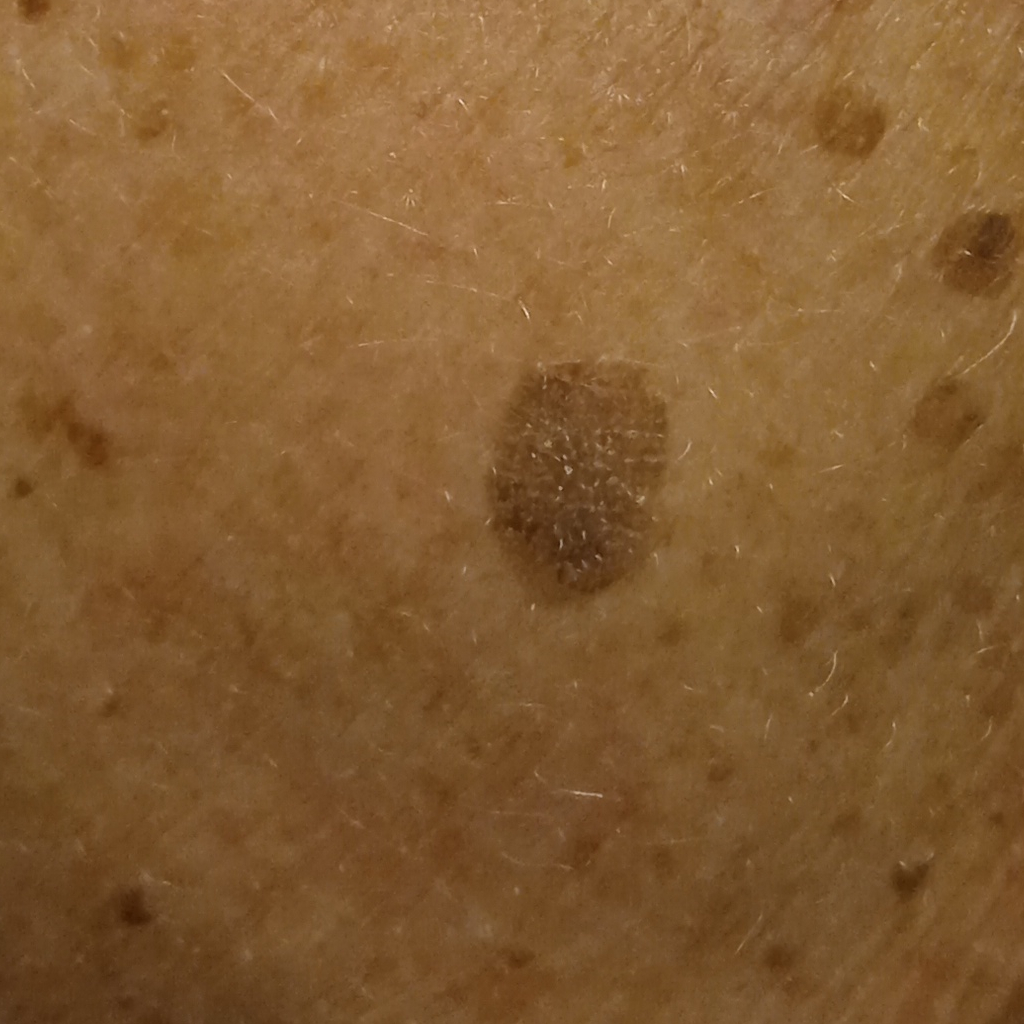Clinical context:
The patient says their skin tans without first burning. A female patient age 78. A clinical close-up of a skin lesion. The patient describes having numerous moles. Collected as part of a research study, without a referral diagnosis. The lesion is located on the back. The lesion is about 9.6 mm across.
Conclusion:
The lesion was assessed as a seborrheic keratosis.